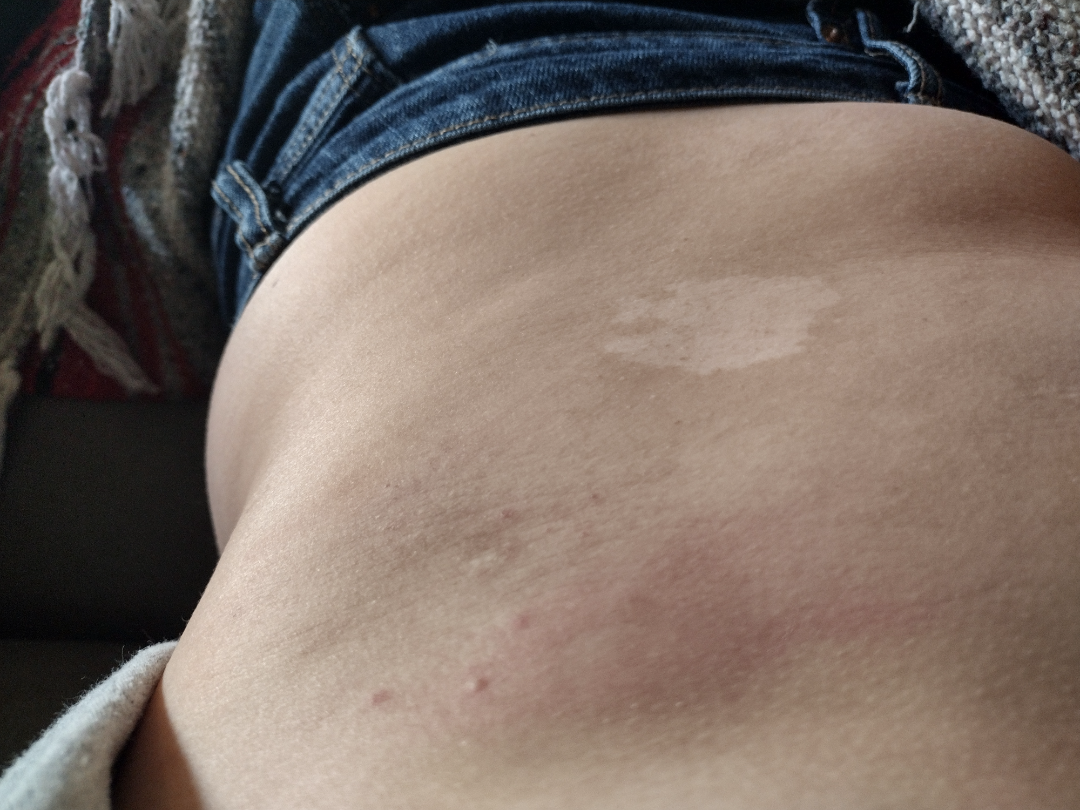Findings:
• view — at an angle
• dermatologist impression — single-reviewer assessment: Pityriasis alba and Melanocytic Nevus were considered with similar weight; lower on the differential is Nevus anemicus